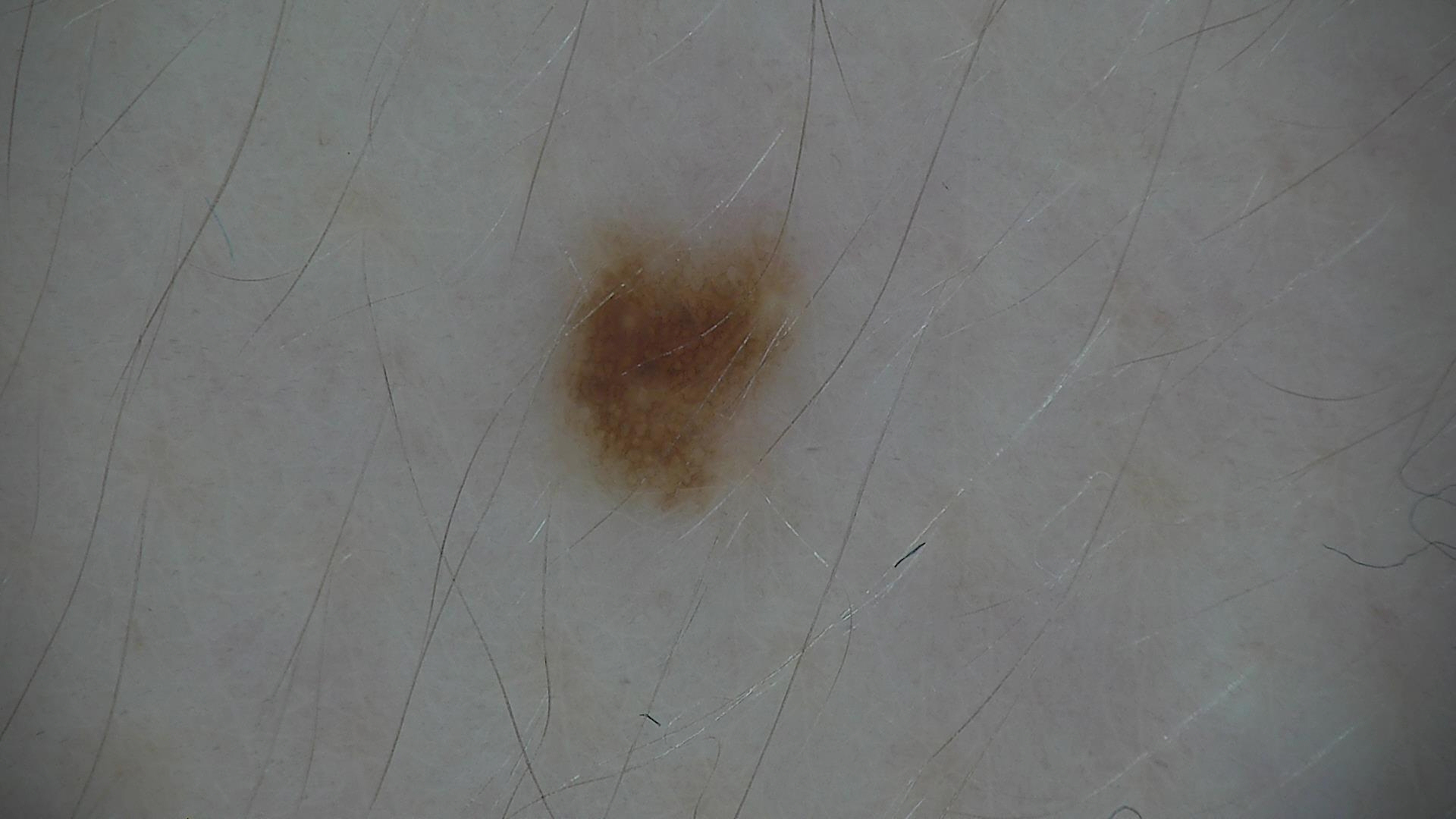Summary: A dermoscopic close-up of a skin lesion. Conclusion: The diagnostic label was a dysplastic junctional nevus.